The patient is Fitzpatrick skin type III · a female patient approximately 55 years of age · a contact-polarized dermoscopy image of a skin lesion: 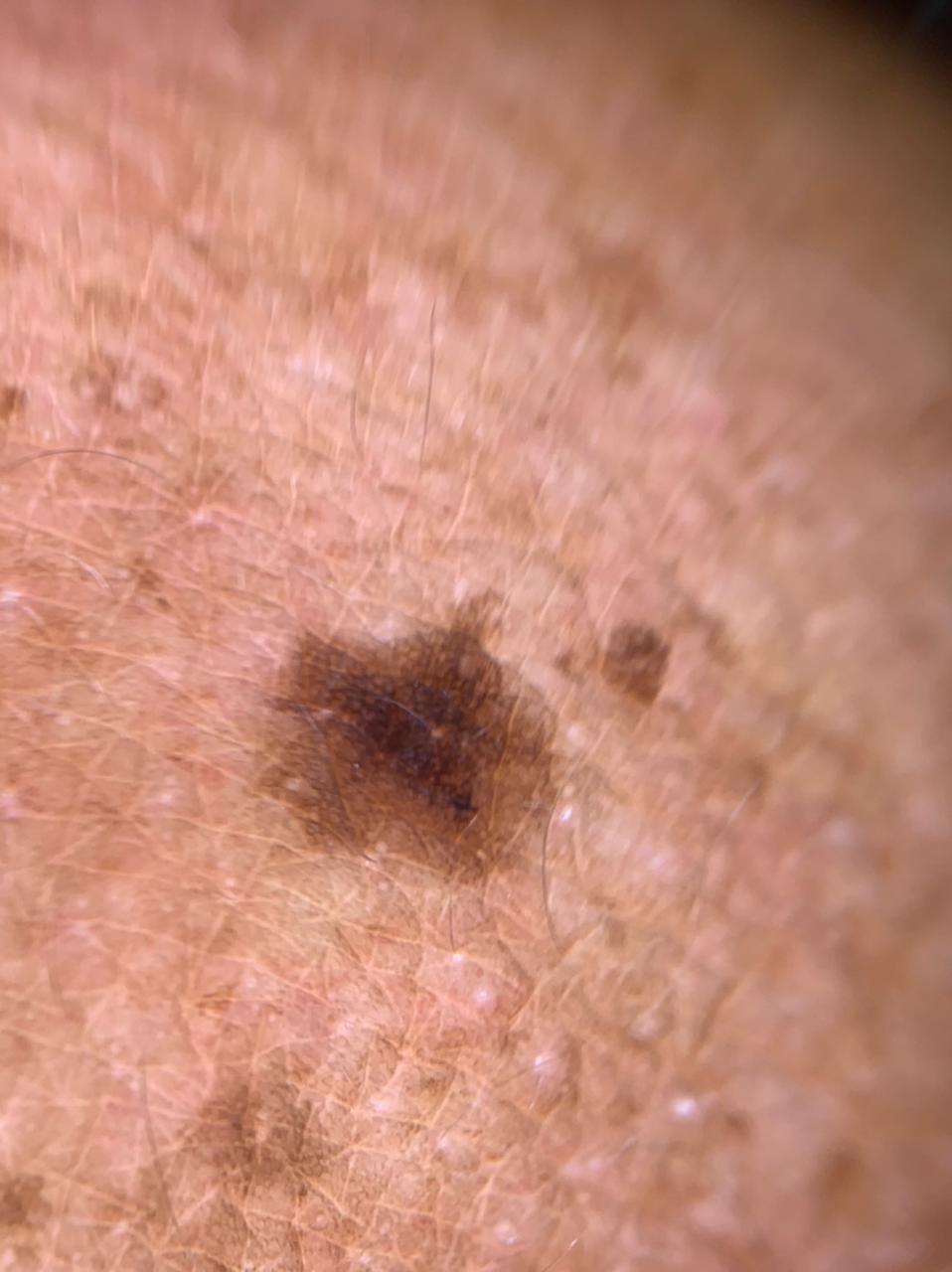assessment=Nevus.